Reported lesion symptoms include enlargement, bothersome appearance and itching · the photograph is a close-up of the affected area · self-categorized by the patient as a rash · the lesion involves the leg · the condition has been present for one to four weeks · the contributor notes the lesion is rough or flaky: 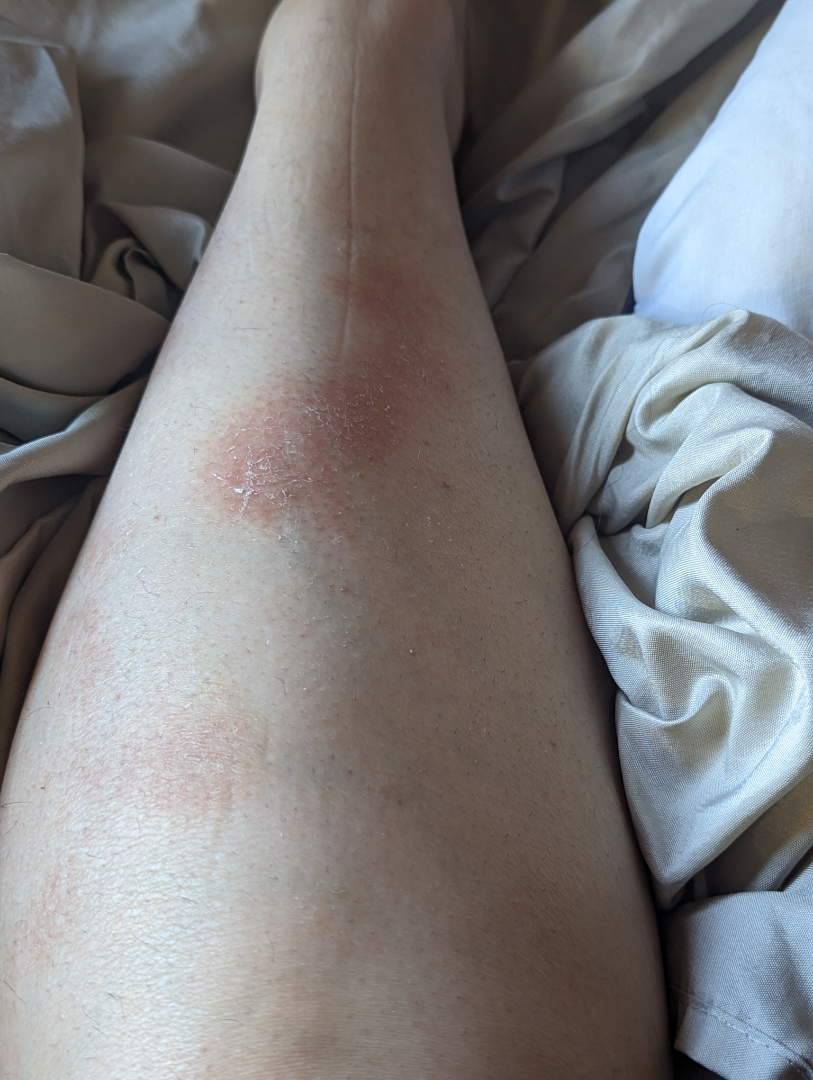Findings:
The differential includes Pigmented purpuric eruption and Erythema nodosum, with no clear leading consideration.